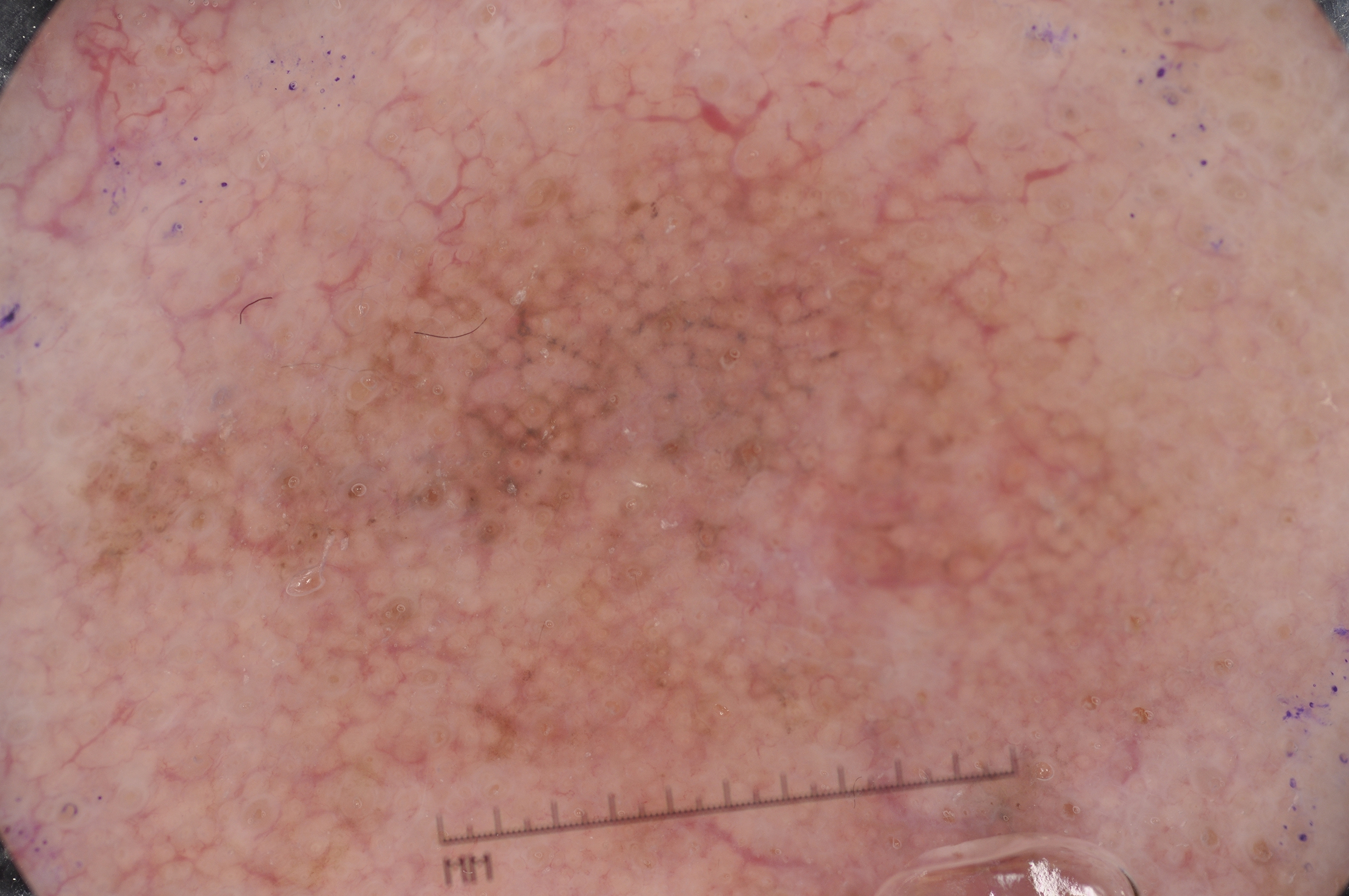Findings:
– subject · male, aged 73-77
– modality · dermoscopic image
– bounding box · 53 22 1270 894
– absent dermoscopic findings · pigment network, milia-like cysts, negative network, and streaks
– extent · large
– impression · a melanoma